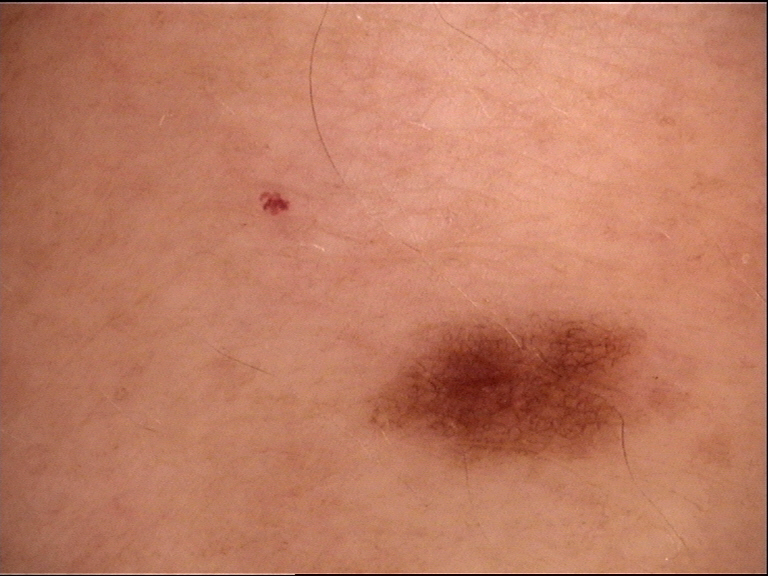A dermoscopy image of a single skin lesion. Diagnosed as a benign lesion — a dysplastic junctional nevus.